The subject is 40–49, female. The back of the torso, arm and front of the torso are involved. An image taken at a distance: 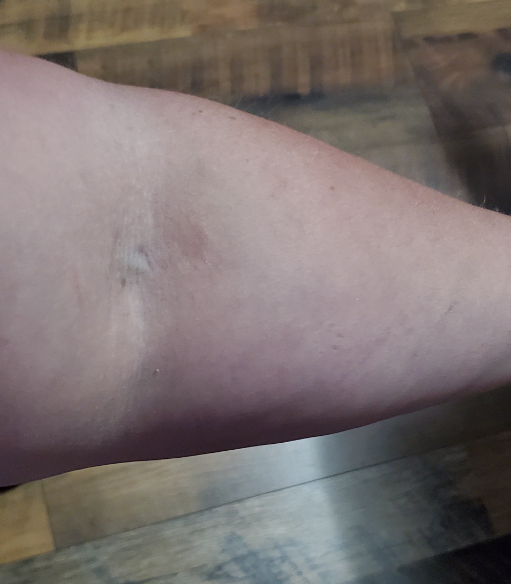Background:
The patient described the issue as a rash. Fitzpatrick skin type IV. Texture is reported as raised or bumpy. The patient notes enlargement and bothersome appearance.
Findings:
On photographic review: Eczema (primary); Acute and chronic dermatitis (possible).